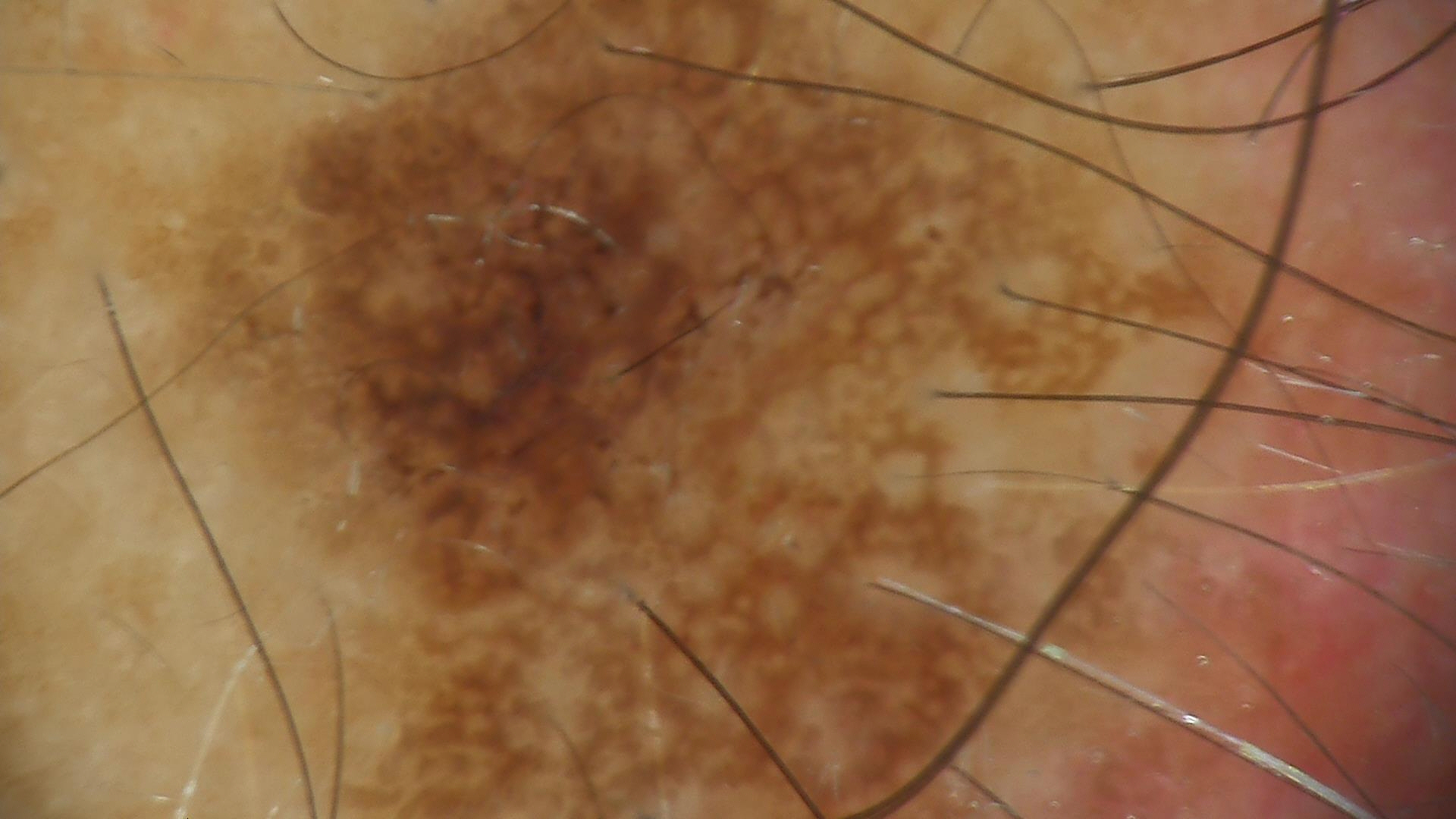{
  "lesion_type": {
    "main_class": "keratinocytic"
  },
  "diagnosis": {
    "name": "seborrheic keratosis",
    "code": "sk",
    "malignancy": "benign",
    "super_class": "non-melanocytic",
    "confirmation": "expert consensus"
  }
}